Reported lesion symptoms include bothersome appearance · reported duration is less than one week · located on the arm · the contributor is 18–29, male · skin tone: FST II · the patient considered this a rash · this image was taken at an angle · texture is reported as rough or flaky and raised or bumpy.
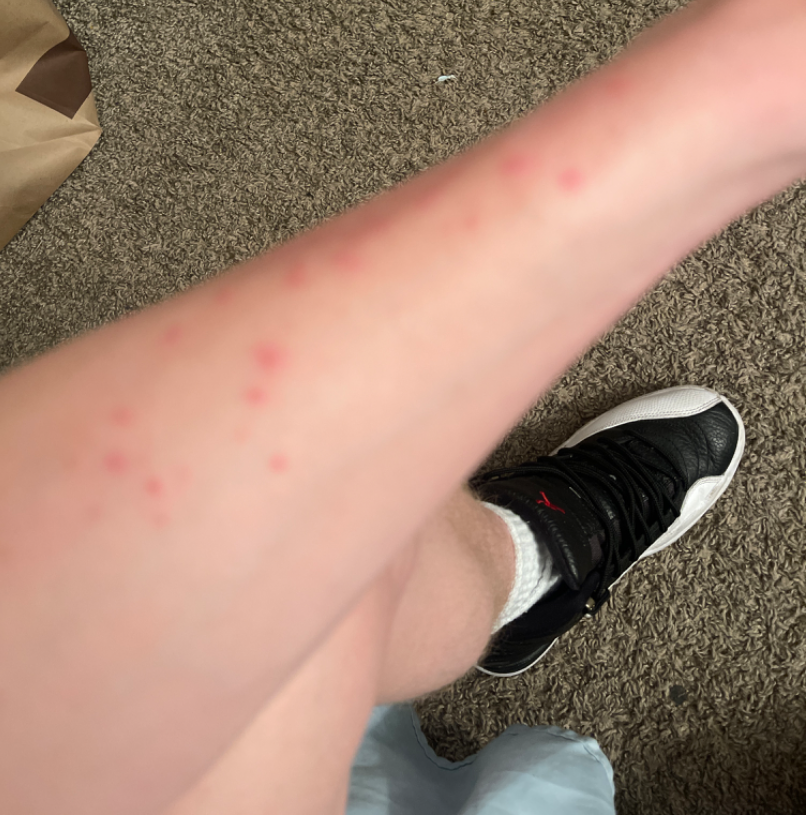Findings:
* dermatologist impression · the leading consideration is Insect Bite; the differential also includes Eczema; possibly Scabies